Dermoscopy of a skin lesion.
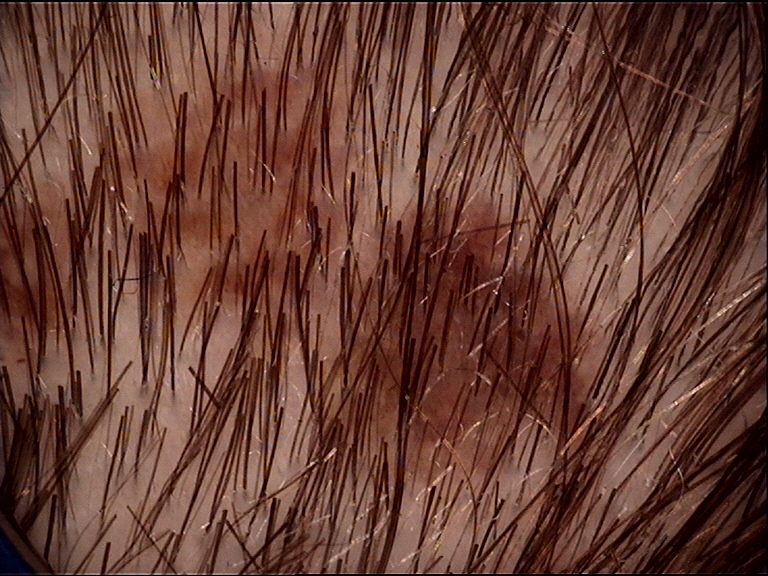{"diagnosis": {"name": "dysplastic junctional nevus", "code": "jd", "malignancy": "benign", "super_class": "melanocytic", "confirmation": "expert consensus"}}